A dermoscopy image of a single skin lesion:
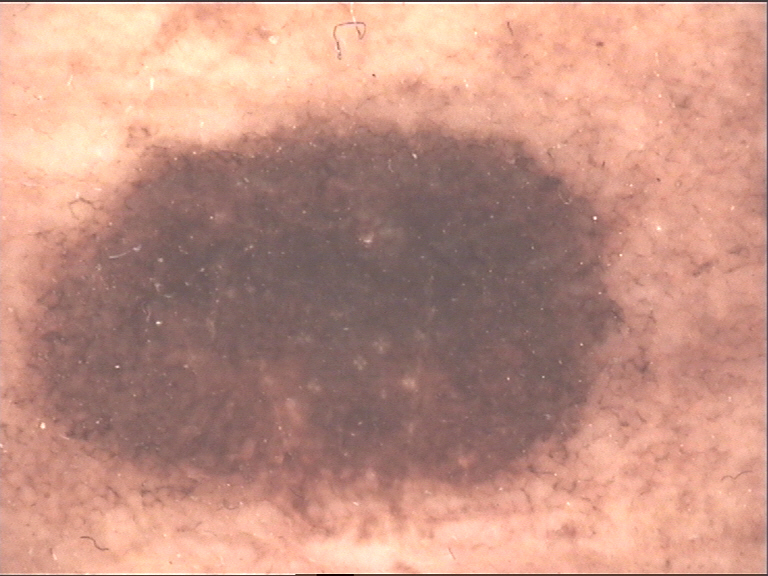Consistent with a banal lesion — a congenital compound nevus.